Reported duration is more than one year · the patient considered this a rash · the photograph is a close-up of the affected area · the lesion is described as rough or flaky, fluid-filled and raised or bumpy · the head or neck is involved · the contributor is 30–39, male · symptoms reported: enlargement, pain, burning, darkening, itching, bleeding and bothersome appearance.
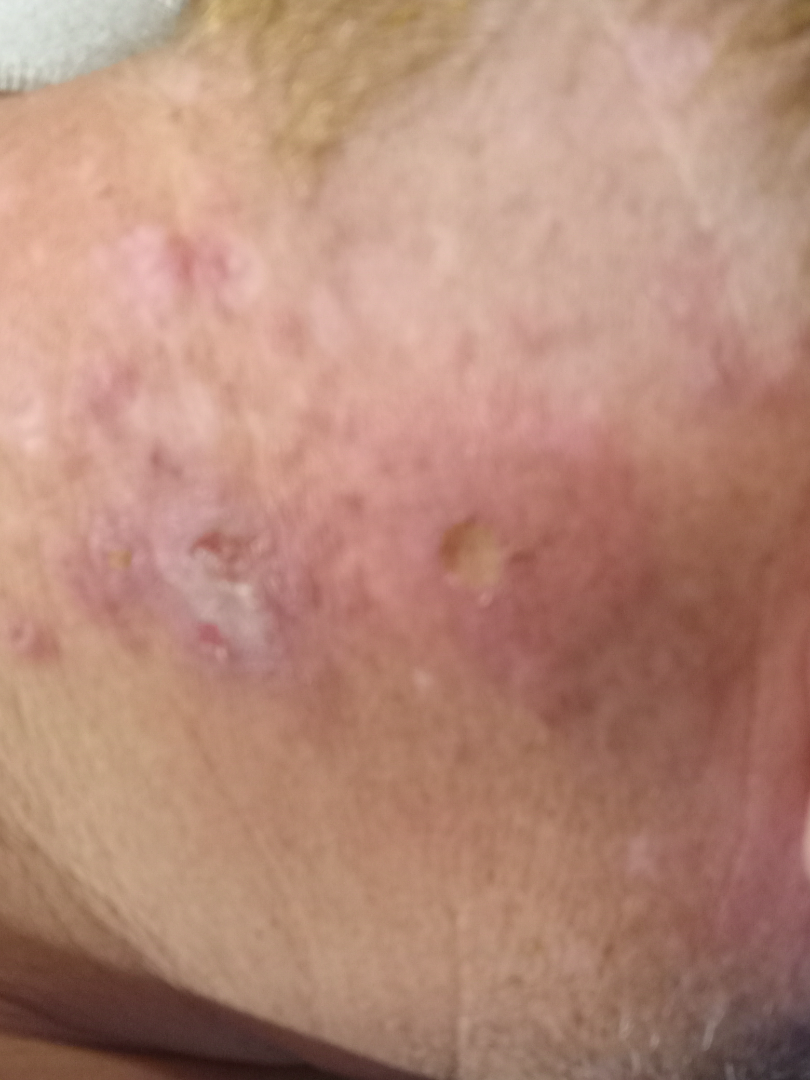Q: What was the assessment?
A: could not be assessed